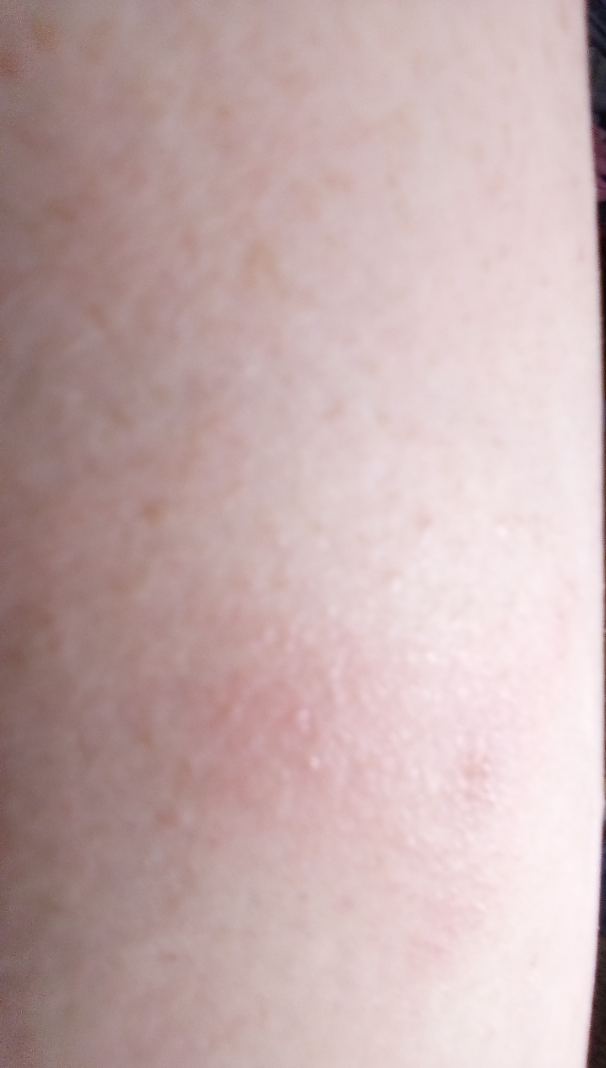Background: Texture is reported as fluid-filled, rough or flaky and raised or bumpy. This image was taken at an angle. Skin tone: Fitzpatrick phototype II; non-clinician graders estimated a Monk skin tone scale of 2. Located on the leg, back of the hand and arm. The patient notes the condition has been present for more than five years. No associated systemic symptoms reported. The patient described the issue as a rash. The contributor is a female aged 40–49. Findings: Most likely Allergic Contact Dermatitis; possibly Hypersensitivity.